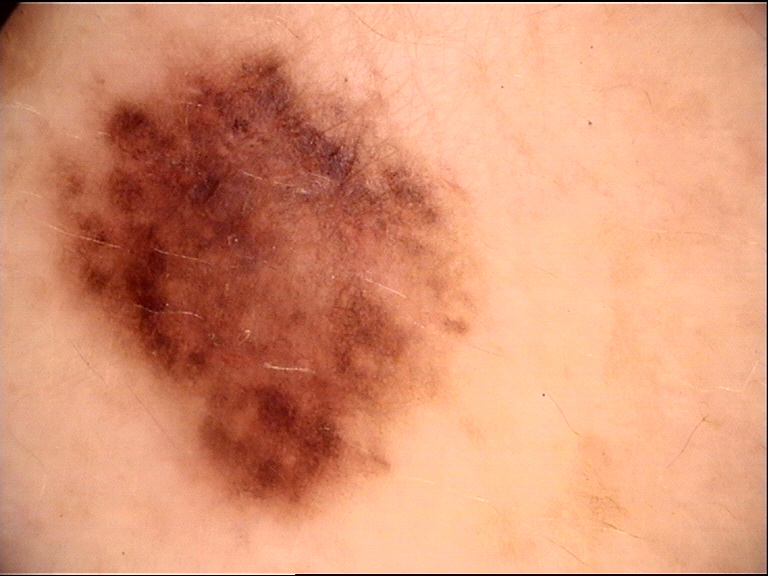modality = dermatoscopy | assessment = dysplastic junctional nevus (expert consensus).